The lesion is described as rough or flaky and raised or bumpy. The patient reports the condition has been present for more than one year. This image was taken at an angle. The patient reports associated joint pain and fatigue. The lesion involves the arm, back of the hand and leg. Self-categorized by the patient as a rash. The lesion is associated with pain, enlargement, itching, darkening, bleeding, bothersome appearance and burning. Female patient, age 50–59 — 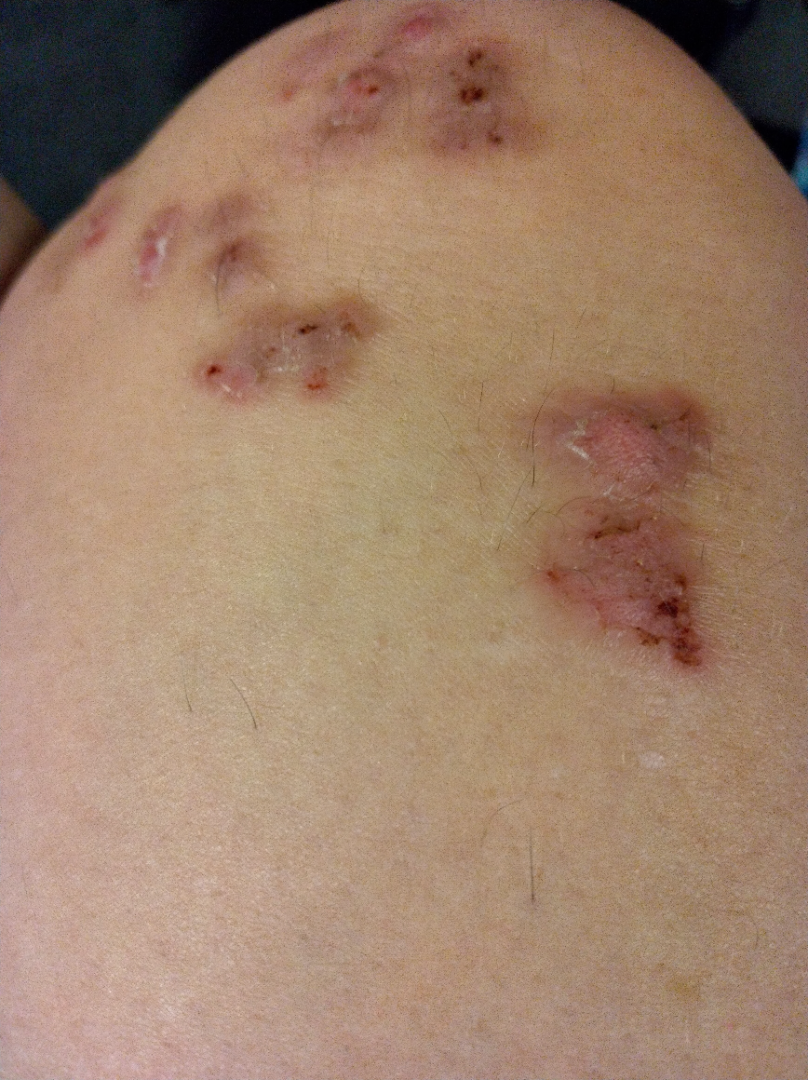Q: Could the case be diagnosed?
A: not assessable